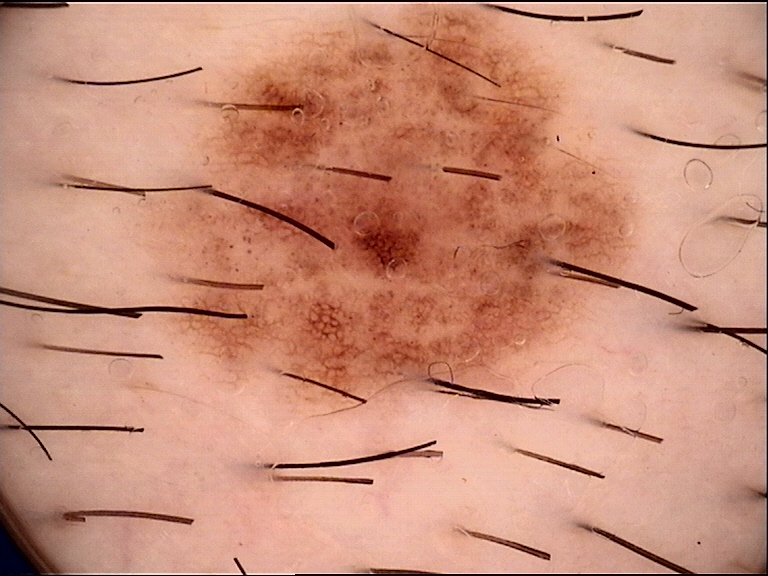A dermoscopic image of a skin lesion. Classified as a dysplastic compound nevus.